A subject 75 years old. A clinical close-up photograph of a skin lesion: 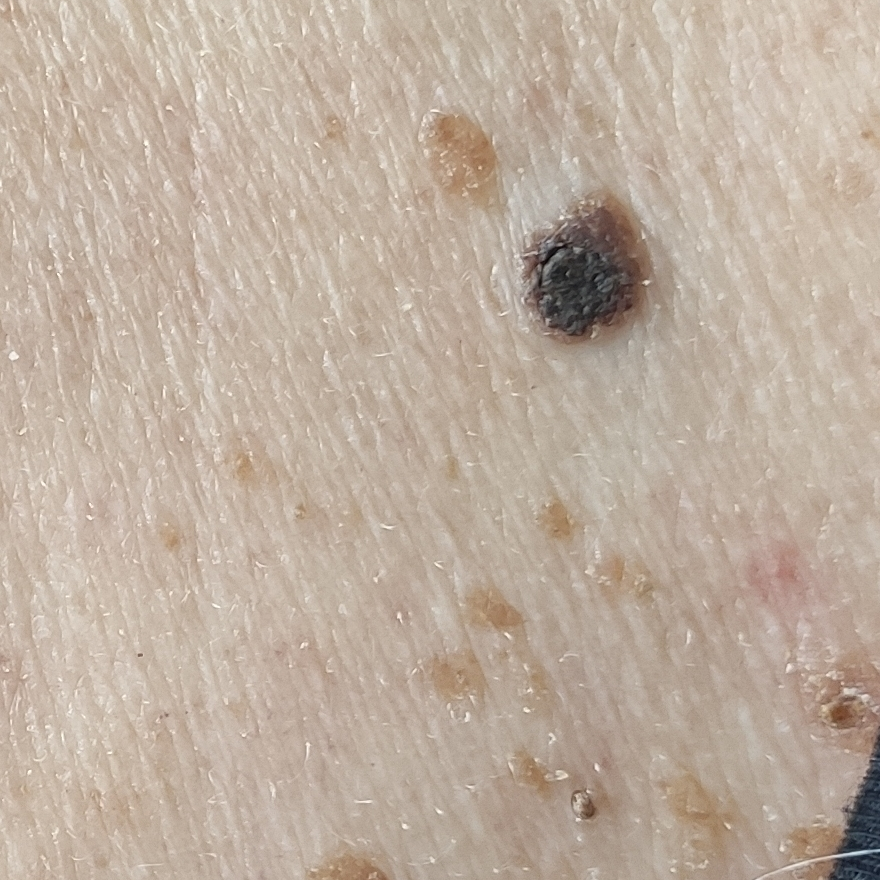The lesion is on the back.
The patient reports that the lesion is elevated, itches, has grown, has bled, and has changed.
The consensus clinical diagnosis was a seborrheic keratosis.